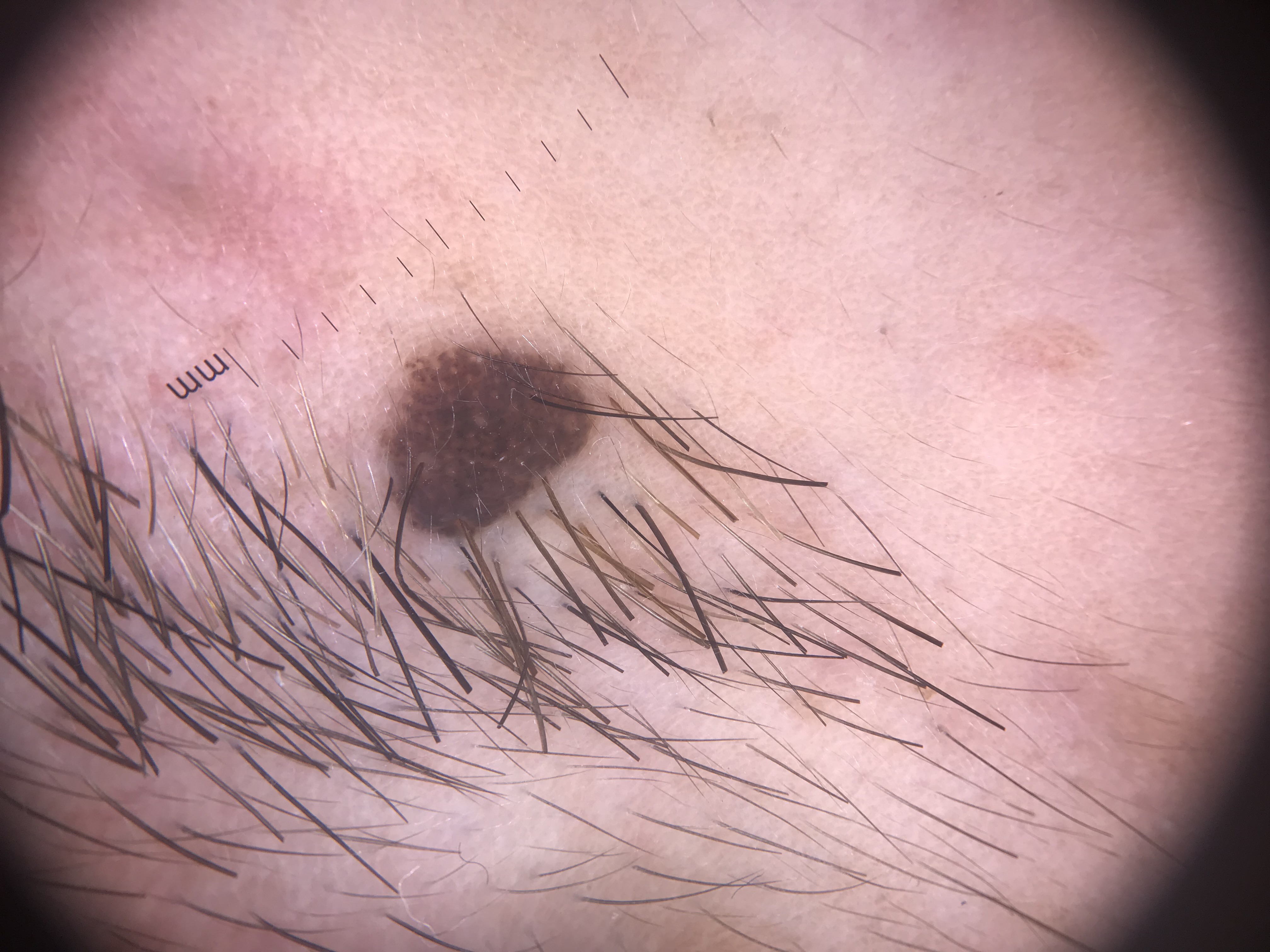A dermoscopic image of a skin lesion.
This is a banal lesion.
Consistent with a compound nevus.